A clinical photograph of a skin lesion · a patient age 54: 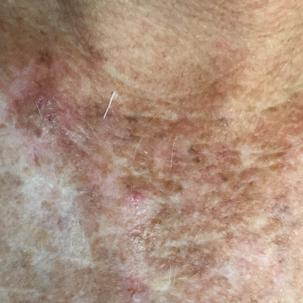Q: What is the anatomic site?
A: the chest
Q: What does the patient describe?
A: bleeding, elevation, itching
Q: What is the diagnosis?
A: actinic keratosis (clinical consensus)